The photograph was taken at an angle — 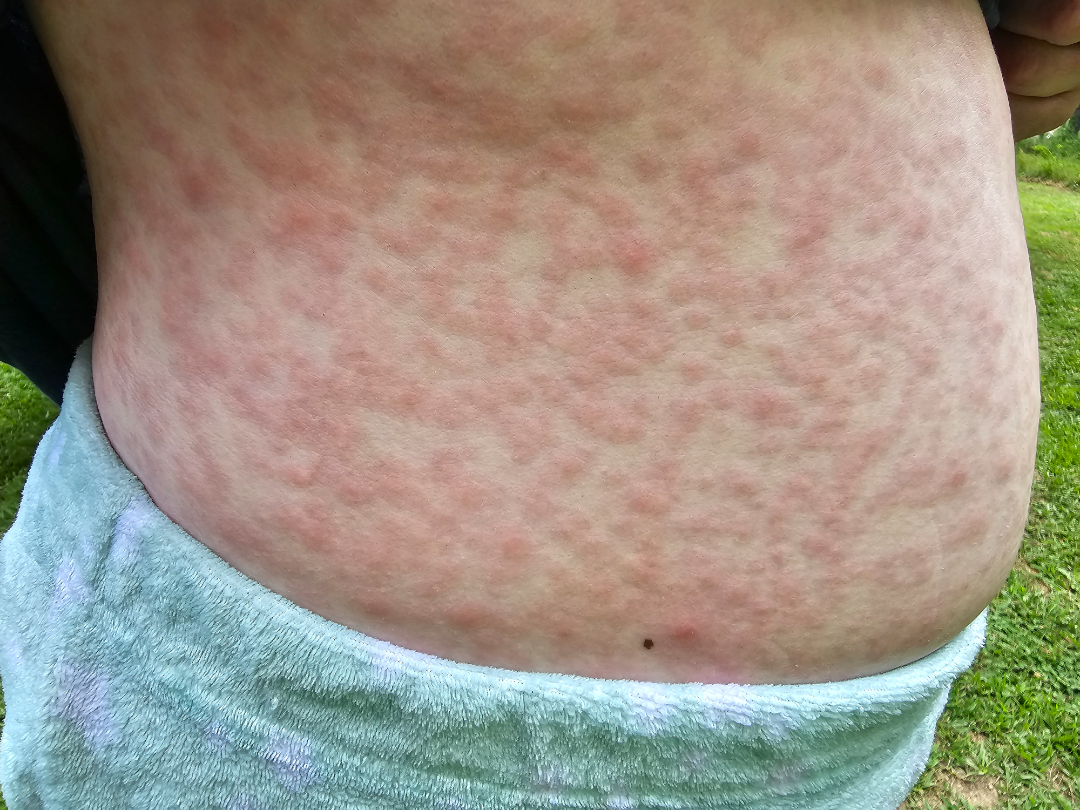assessment — unable to determine.